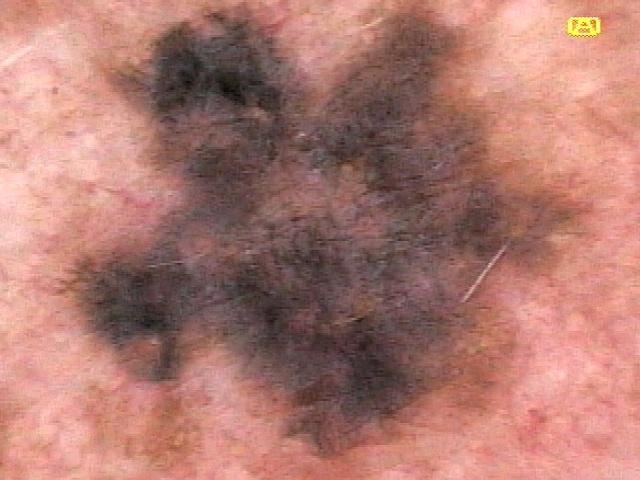Recorded as Fitzpatrick phototype II.
A male subject about 75 years old.
Contact-polarized dermoscopy of a skin lesion.
The chart notes a prior melanoma.
The lesion was found on the trunk, specifically the posterior trunk.
On biopsy, the diagnosis was a melanoma.